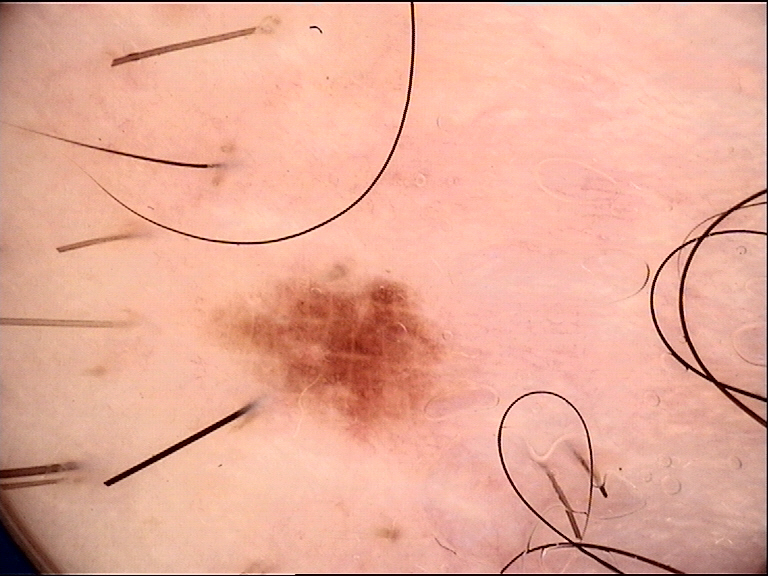Conclusion: Diagnosed as a benign lesion — a dysplastic junctional nevus.